Dermoscopy of a skin lesion: 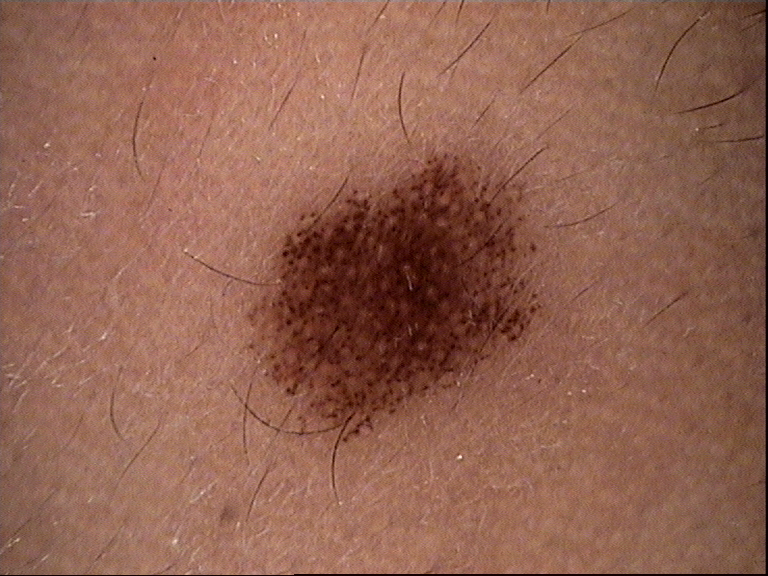<case>
<diagnosis>
<name>dysplastic junctional nevus</name>
<code>jd</code>
<malignancy>benign</malignancy>
<super_class>melanocytic</super_class>
<confirmation>expert consensus</confirmation>
</diagnosis>
</case>